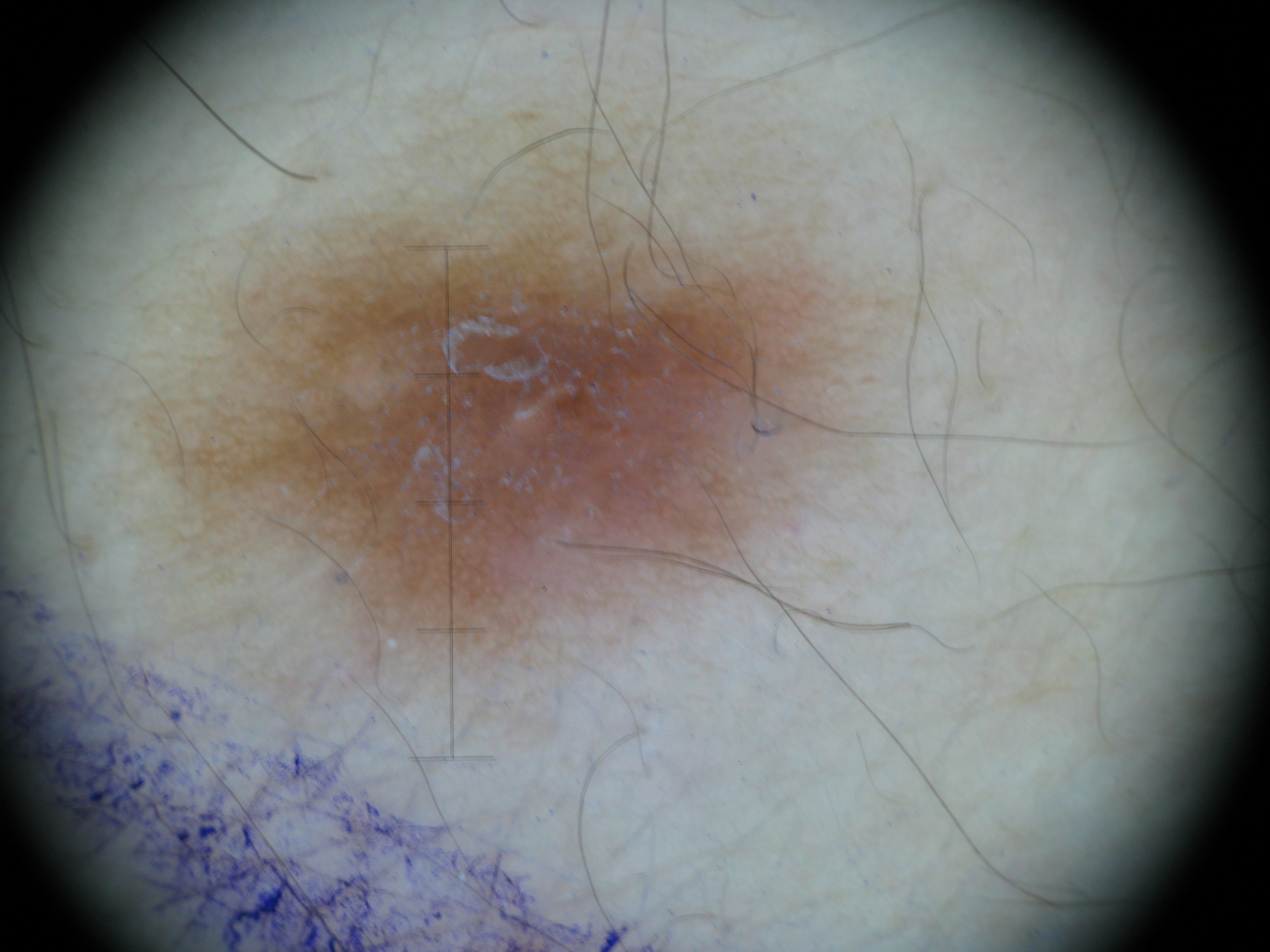This is a fibro-histiocytic lesion.
Diagnosed as a benign lesion — a dermatofibroma.